Dermoscopy of a skin lesion.
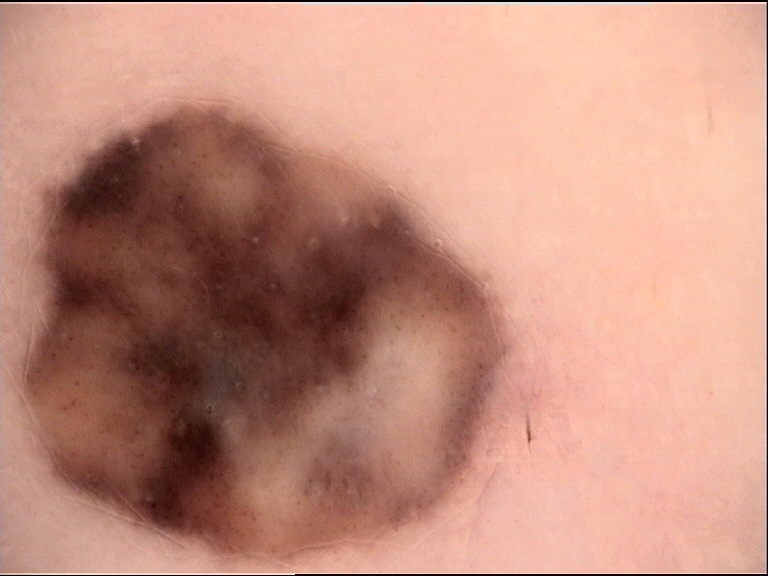label: blue nevus (expert consensus).